The lesion involves the leg. The condition has been present for less than one week. The photo was captured at a distance. The contributor is 30–39, male. The contributor reports itching.
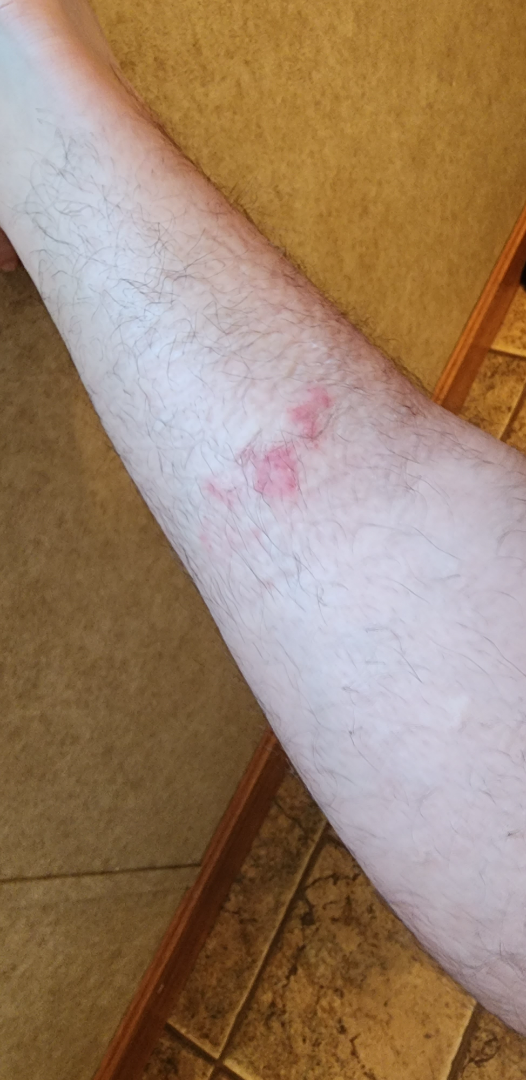impression = Allergic Contact Dermatitis (considered); Irritant Contact Dermatitis (considered)